The photo was captured at an angle:
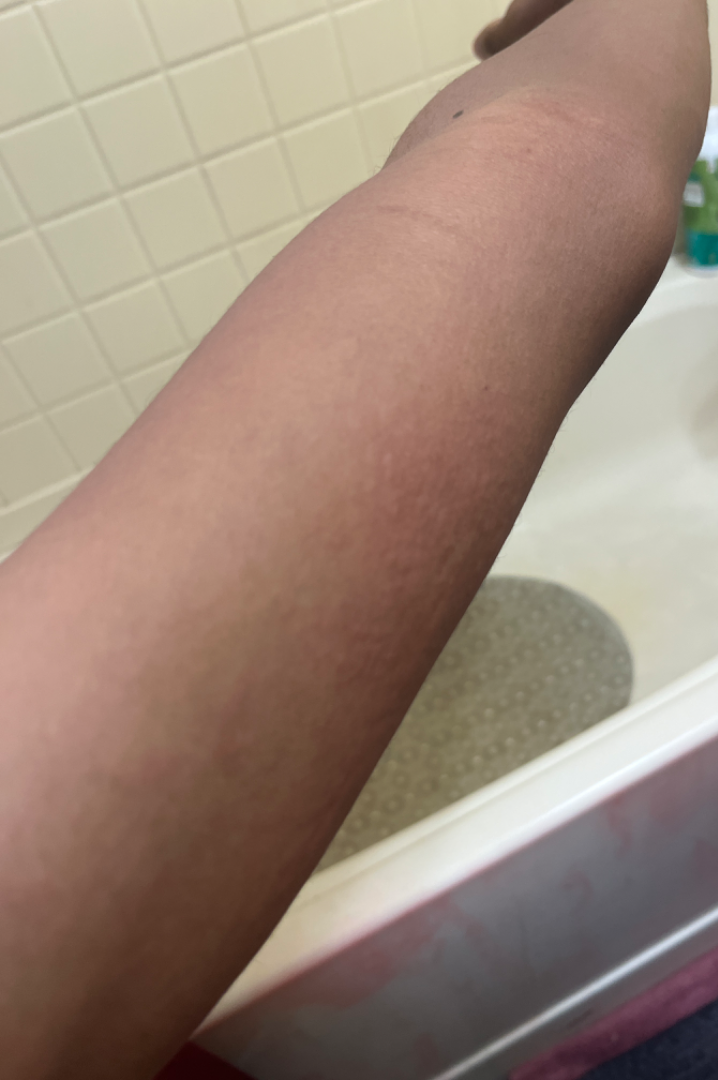assessment — not assessable.